FST I; lay graders estimated 2 on the Monk Skin Tone. An image taken at an angle — 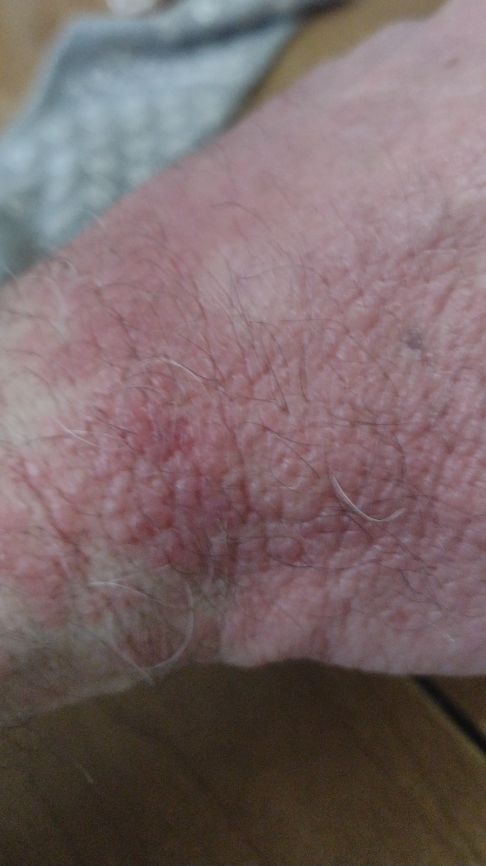impression = Eczema (considered); Allergic Contact Dermatitis (considered)